A clinical photograph showing a skin lesion — 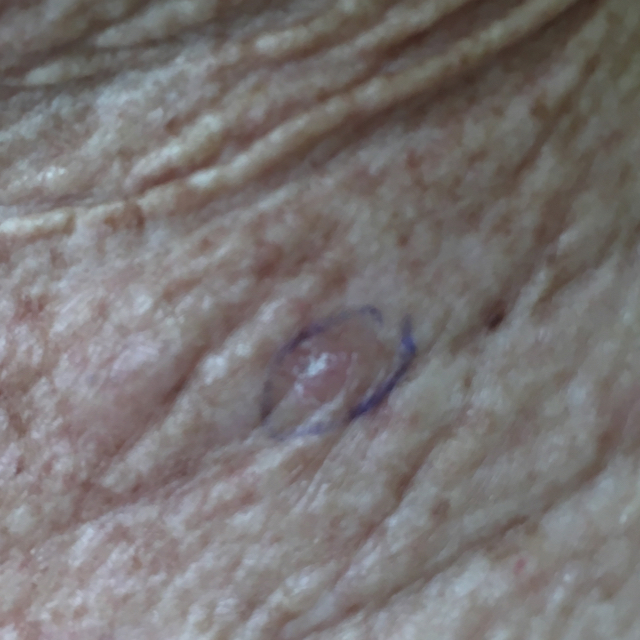  lesion_location: the chest
  diagnosis:
    name: actinic keratosis
    code: ACK
    malignancy: indeterminate
    confirmation: clinical consensus